A dermoscopic image of a skin lesion: 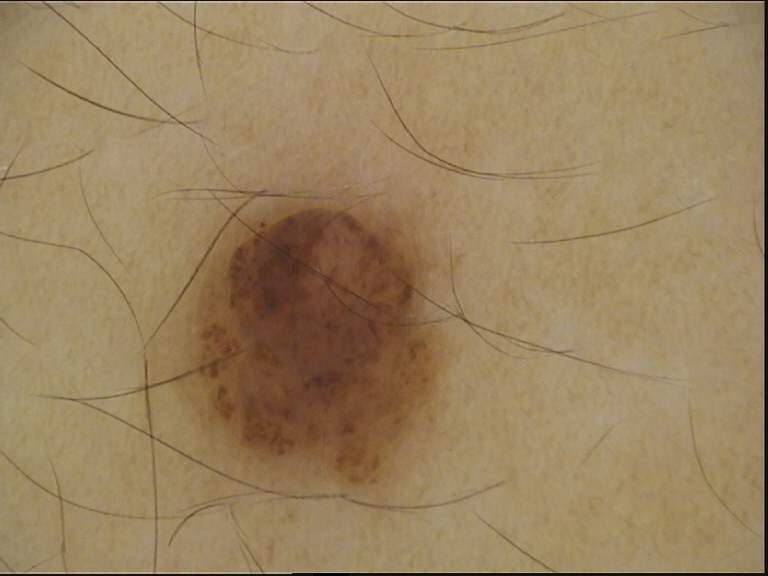Labeled as a compound nevus.